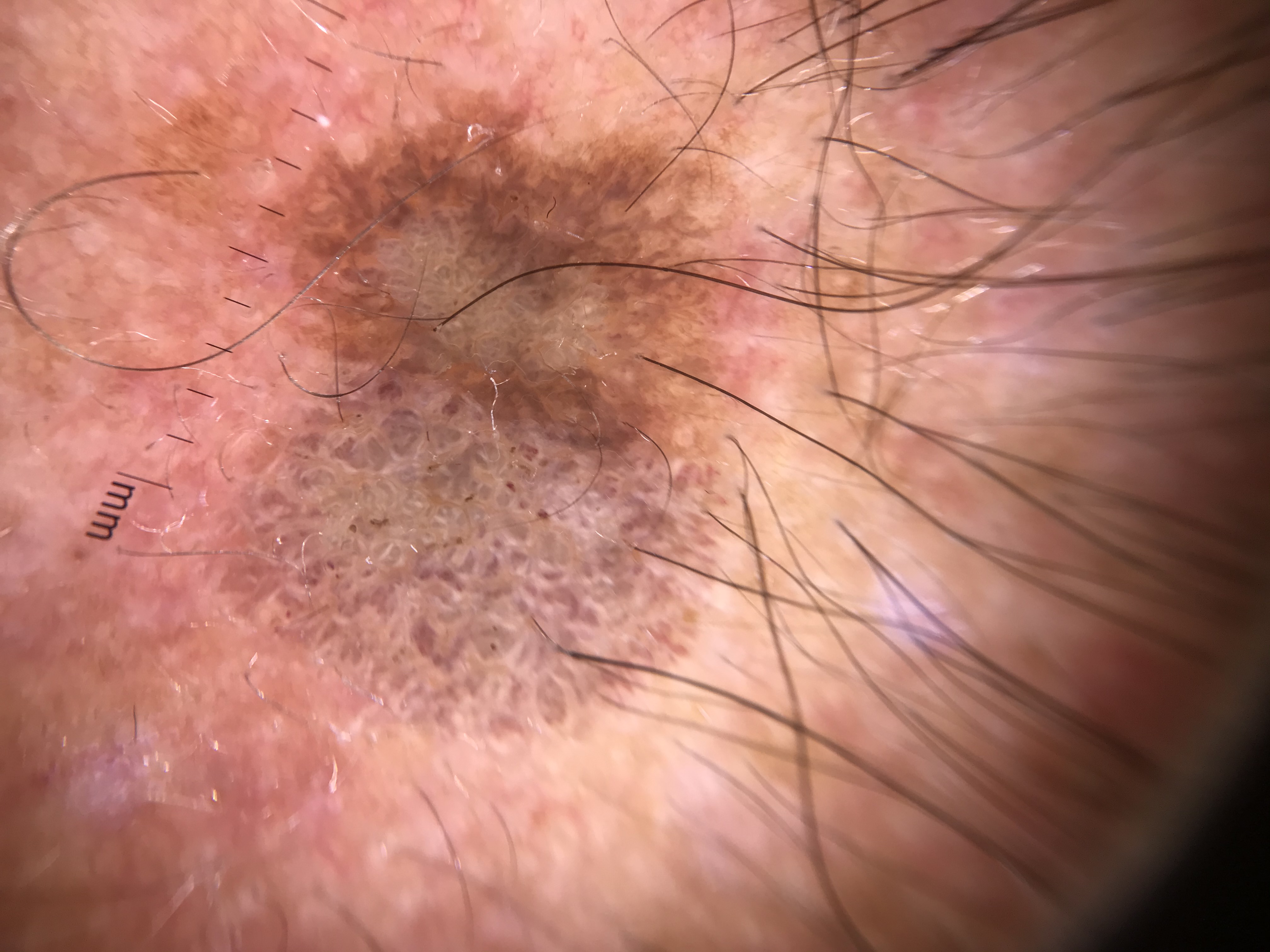imaging = dermoscopy, class = seborrheic keratosis (expert consensus).